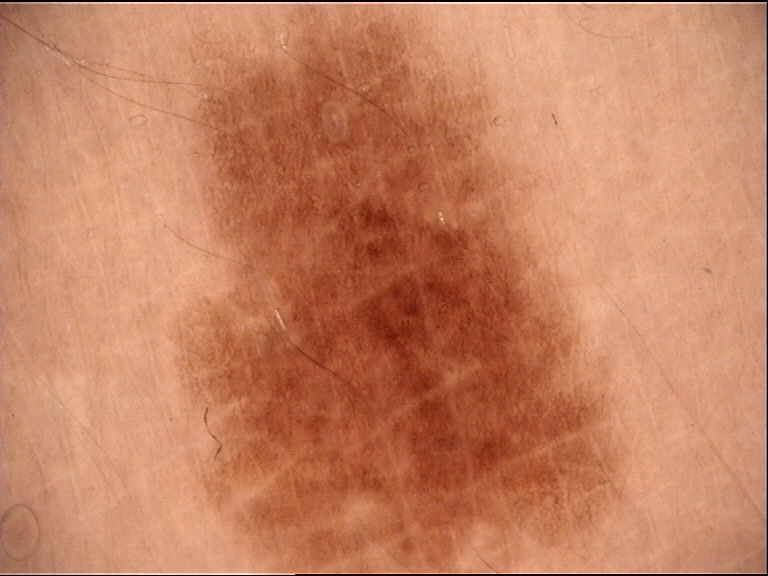A dermoscopy image of a single skin lesion.
Diagnosed as a dysplastic junctional nevus.